A dermatoscopic image of a skin lesion:
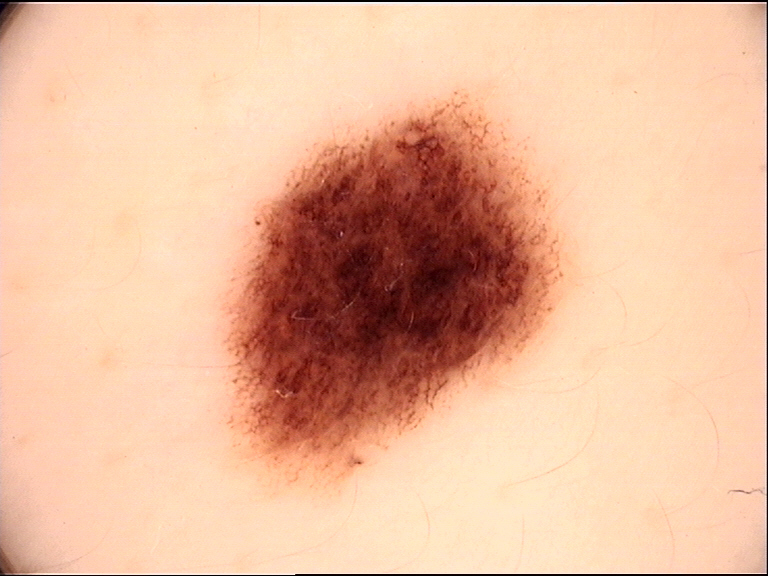Consistent with a benign lesion — a dysplastic junctional nevus.